Located on the back of the hand; this image was taken at an angle; the patient is a female aged 30–39 — 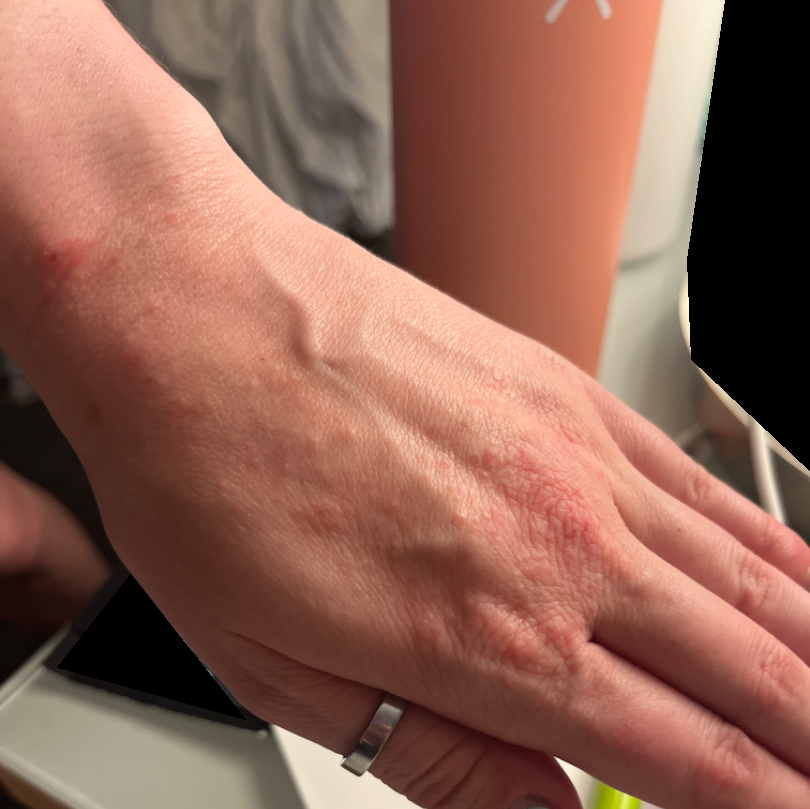<dermatology_case>
<differential>
  <leading>Allergic Contact Dermatitis</leading>
  <considered>Eczema, Irritant Contact Dermatitis</considered>
</differential>
</dermatology_case>